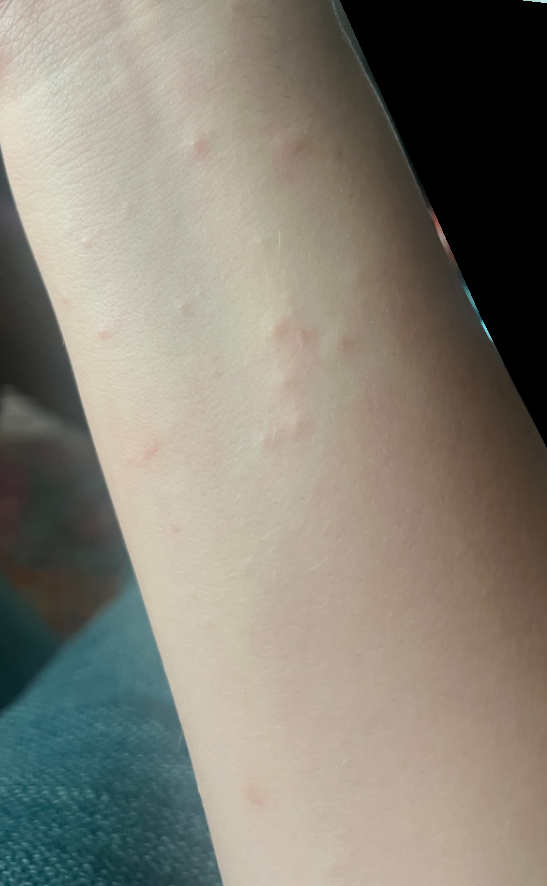Impression: On photographic review, the differential, in no particular order, includes Urticaria and Acute dermatitis, NOS.